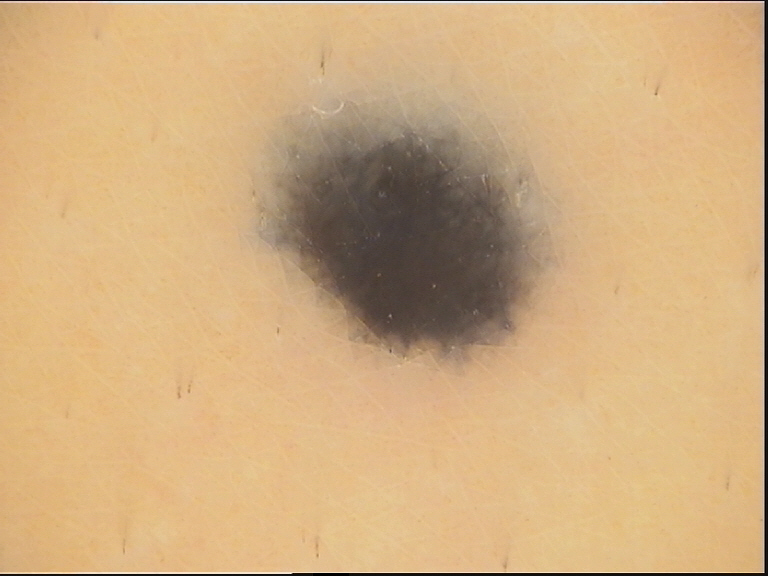A dermoscopy image of a single skin lesion. The diagnostic label was a banal lesion — a blue nevus.